The photo was captured at a distance. Fitzpatrick phototype III — 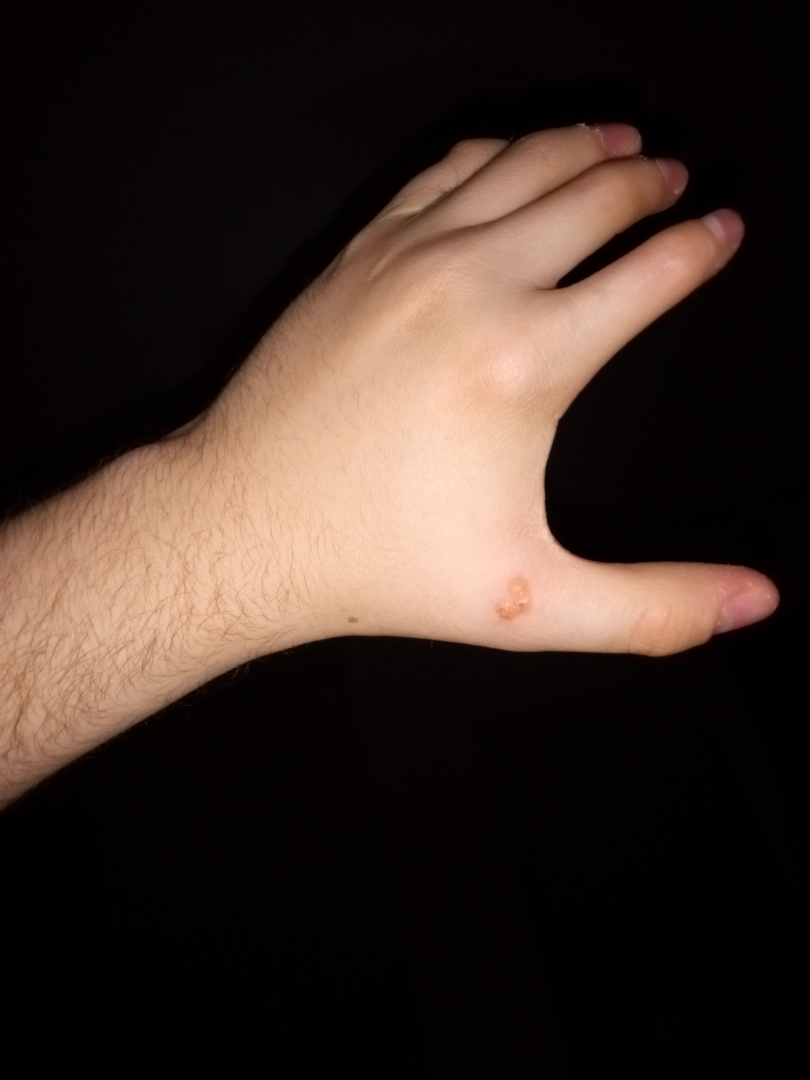Impression: On photographic review by a dermatologist, Impetigo (weight 0.33); Molluscum Contagiosum (weight 0.33); Herpes Simplex (weight 0.33).